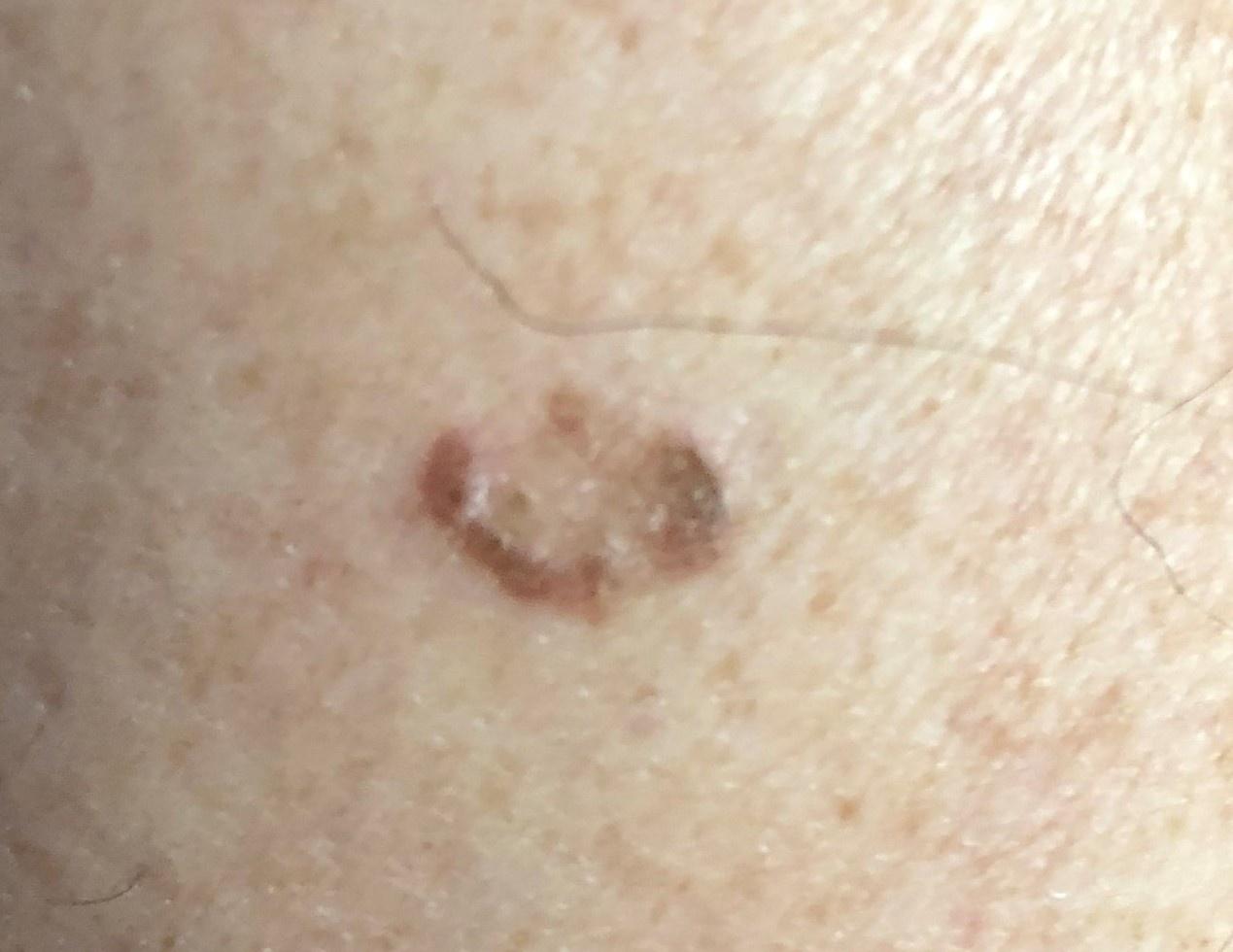Notes:
- imaging · clinical photograph
- subject · female, approximately 70 years of age
- skin type · II
- body site · a lower extremity
- assessment · Seborrheic keratosis